A dermoscopic close-up of a skin lesion: 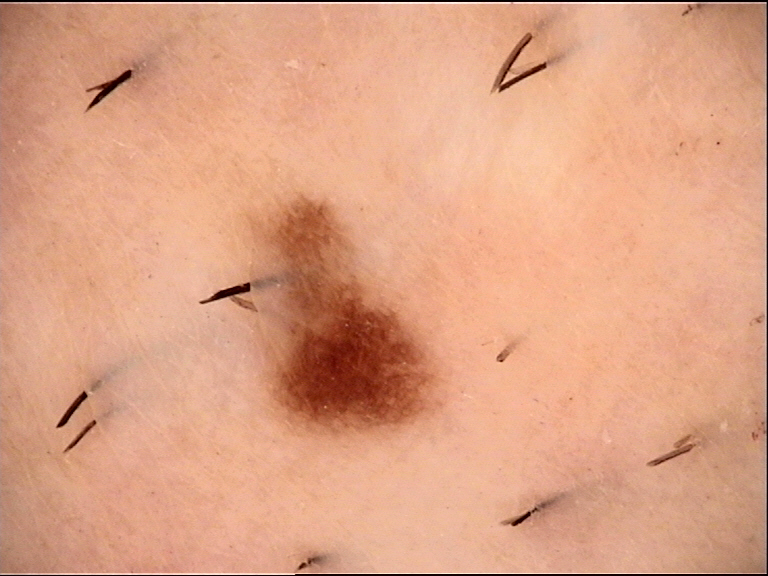Classified as a benign lesion — a dysplastic junctional nevus.